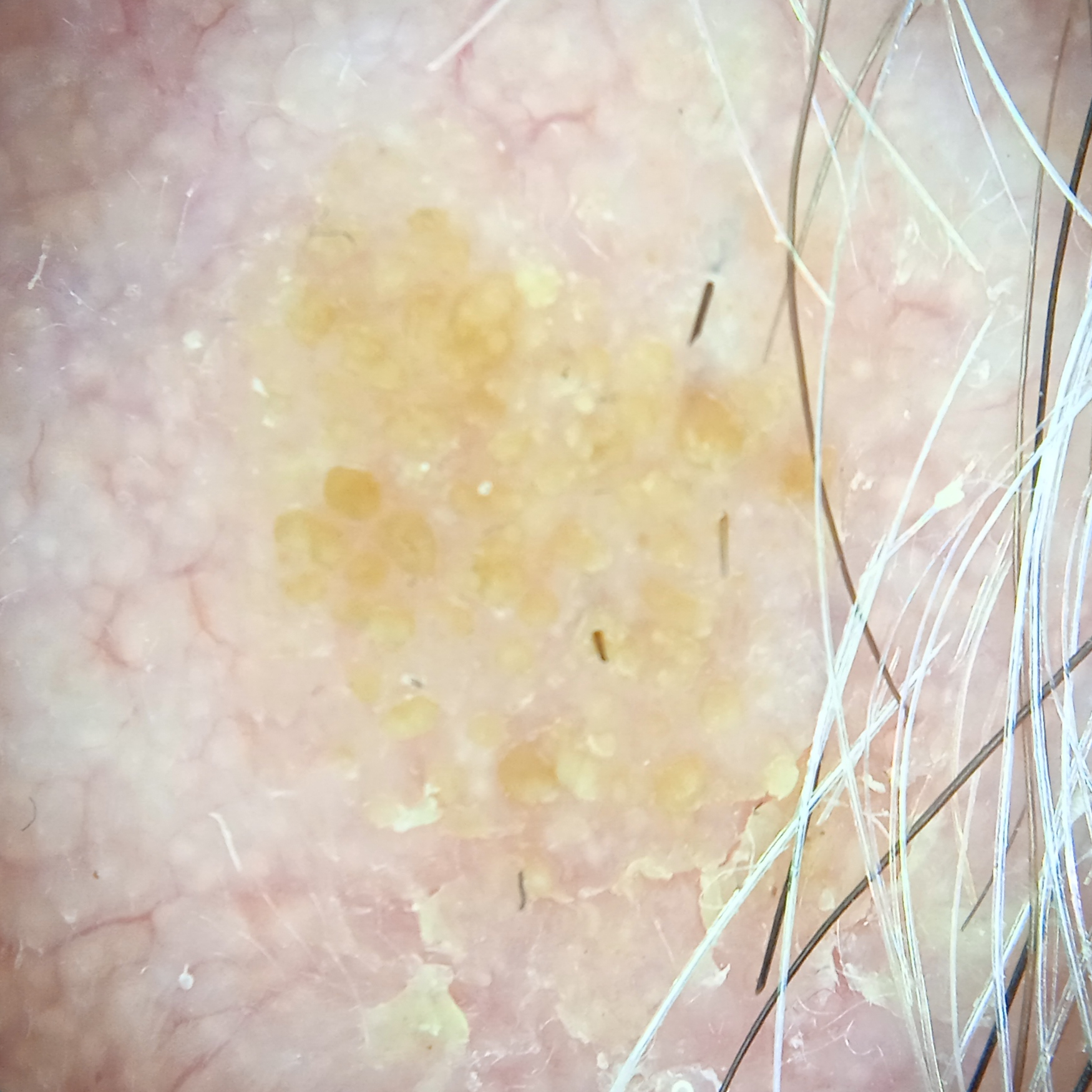Findings:
– subject — male, age 89
– sun reaction — skin reddens painfully with sun exposure
– relevant history — no sunbed use
– location — the face
– diameter — 8.8 mm
– diagnostic label — seborrheic keratosis (dermatologist consensus)